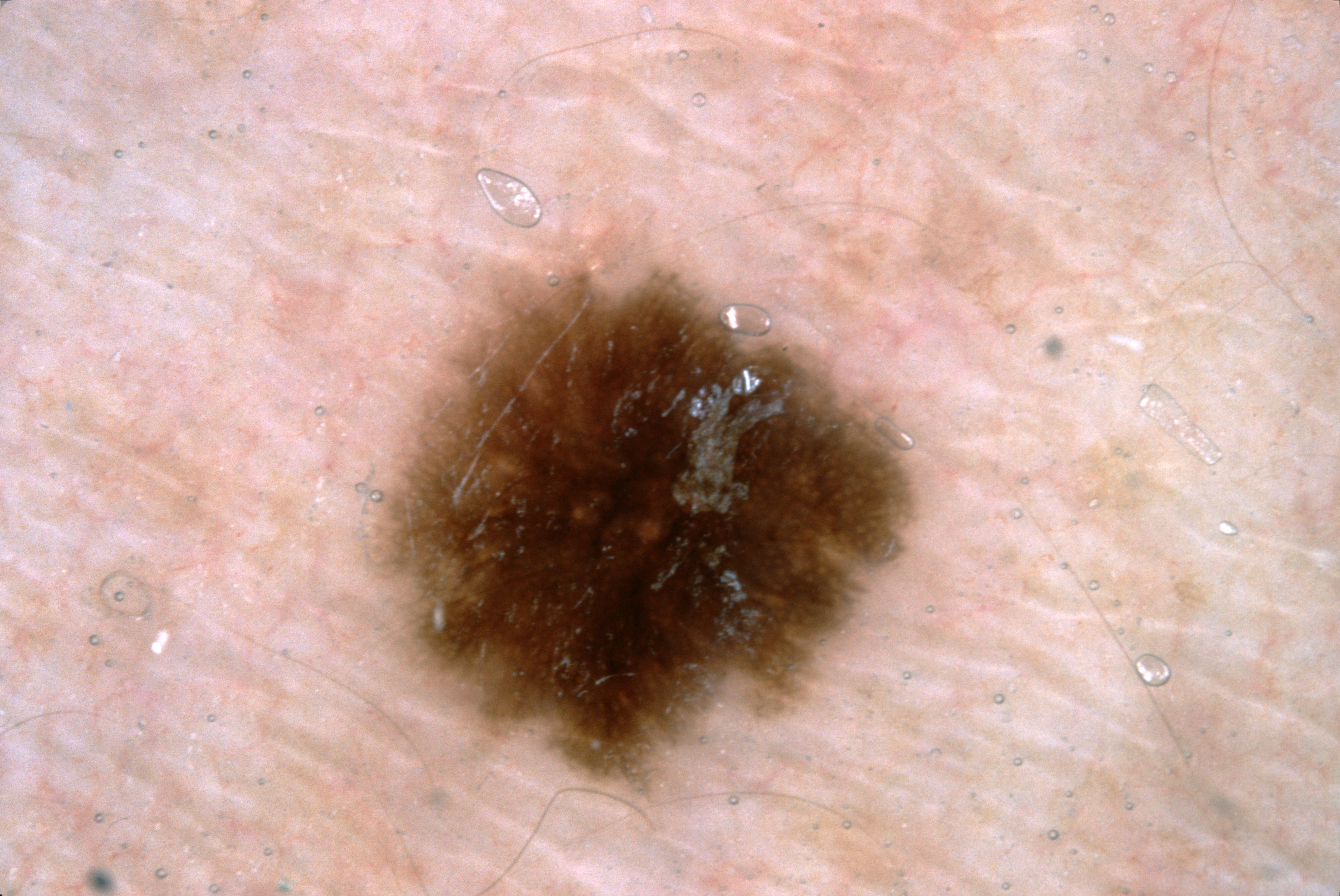A skin lesion imaged with a dermatoscope. A female subject aged approximately 50. Dermoscopic assessment notes pigment network. The lesion's extent is box(376, 267, 915, 793). The lesion takes up about 16% of the image. Diagnosed as a melanocytic nevus.